A dermoscopy image of a single skin lesion.
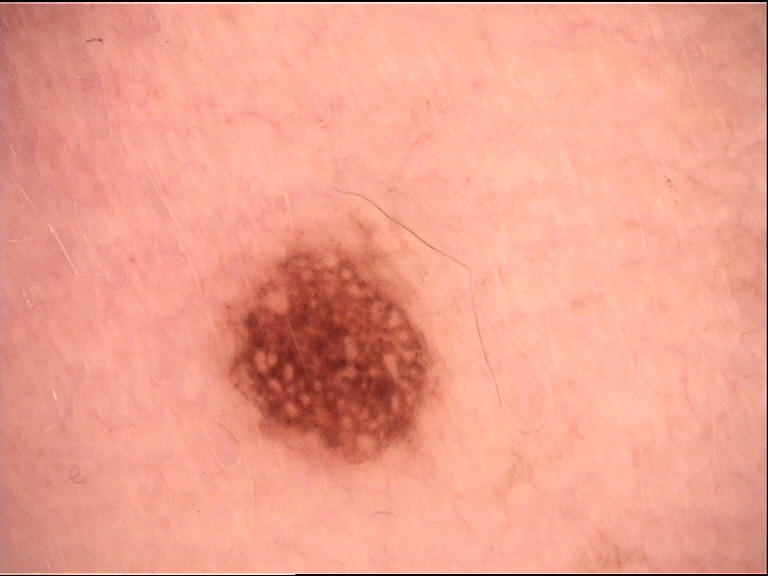Findings: This is a banal lesion. Conclusion: The diagnostic label was a compound nevus.